Dermoscopy of a skin lesion: 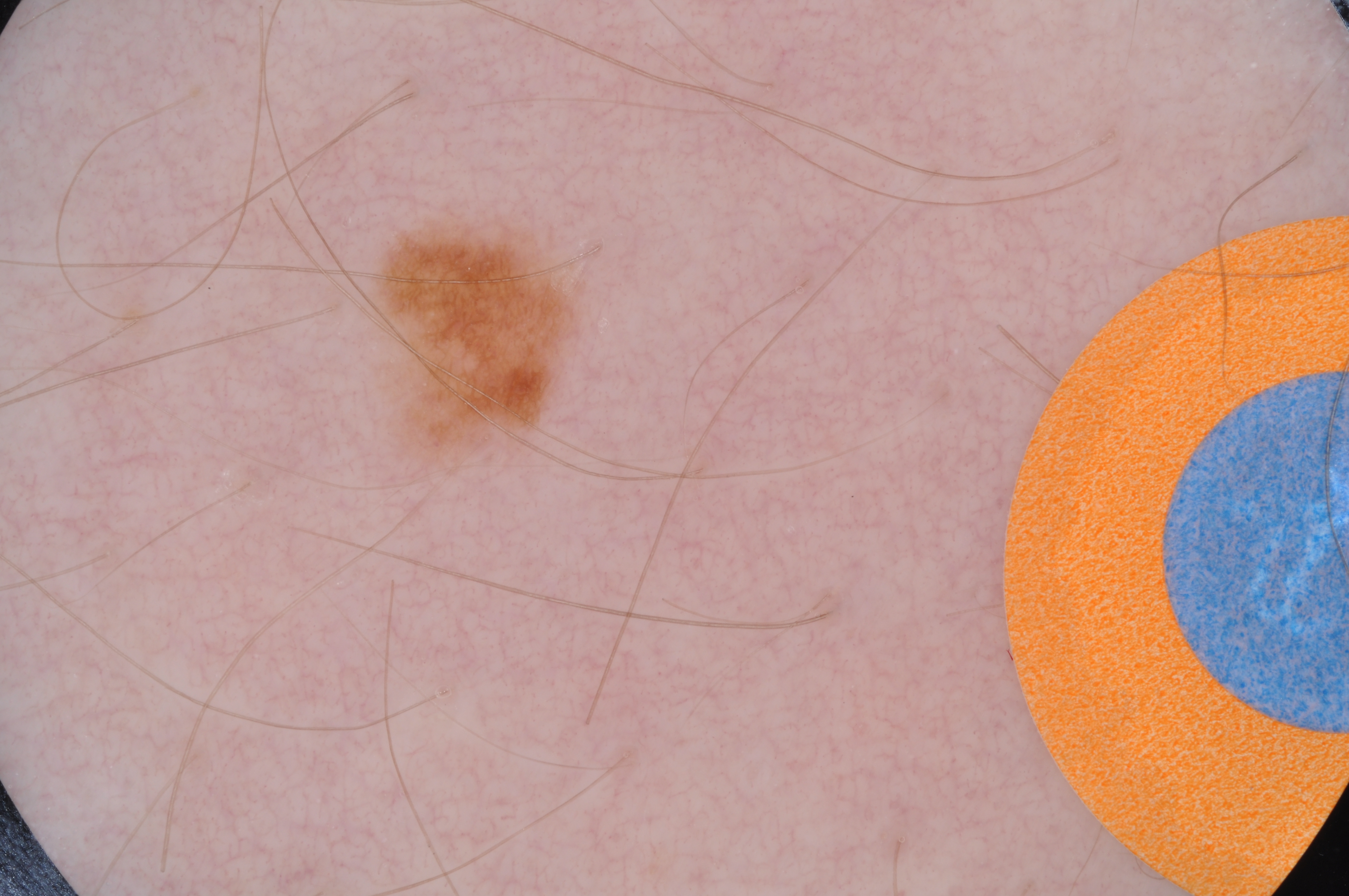Dermoscopically, the lesion shows neither globules nor streaks.
The lesion is located at x1=362 y1=206 x2=599 y2=461.
The lesion covers approximately 4% of the dermoscopic field.
Clinically diagnosed as a benign lesion.